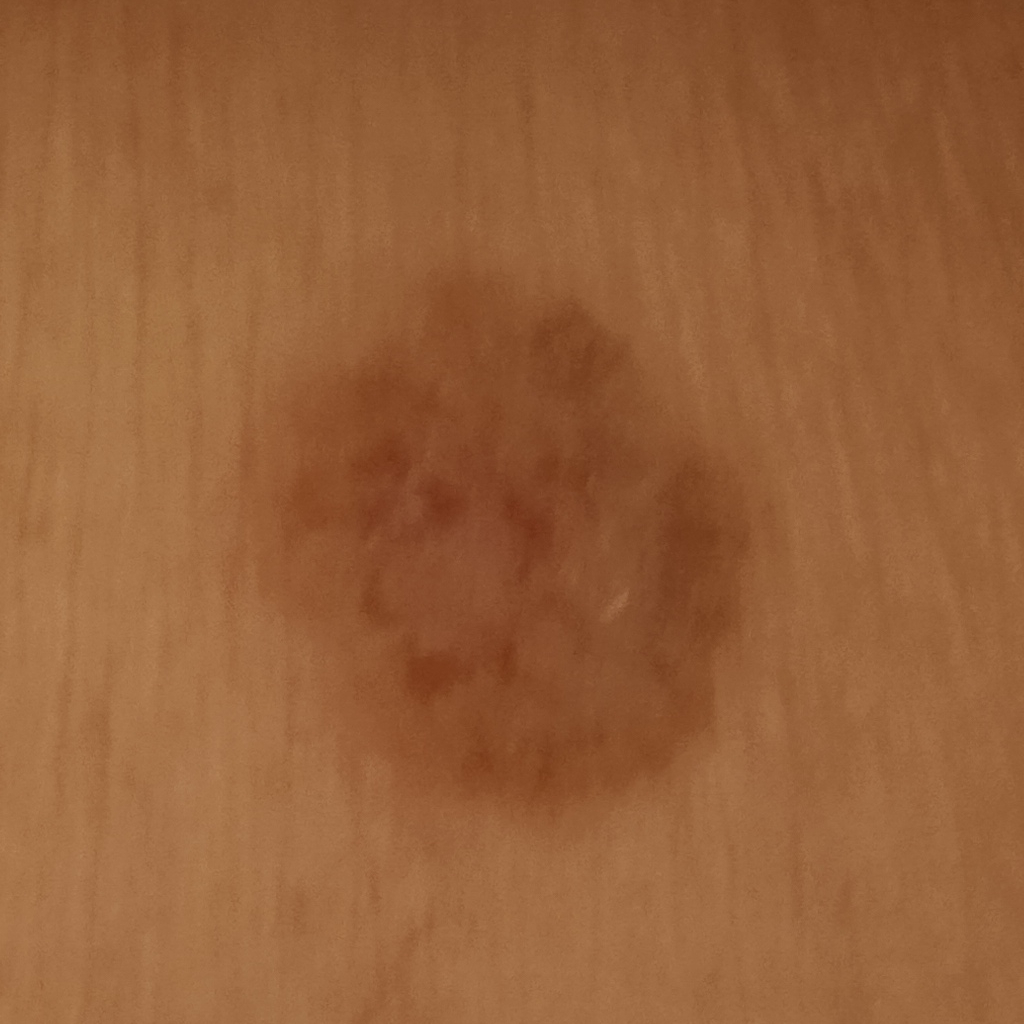Clinical context: A female patient 60 years of age. The patient says their skin tans without first burning. Few moles overall by the patient's own estimate. A macroscopic clinical photograph of a skin lesion. On a questionnaire the patient reported a personal history of skin cancer and a personal history of cancer. Referred with a clinical suspicion of basal cell carcinoma. The lesion involves the torso. The lesion measures approximately 13.2 mm. Conclusion: The diagnostic impression was a basal cell carcinoma.